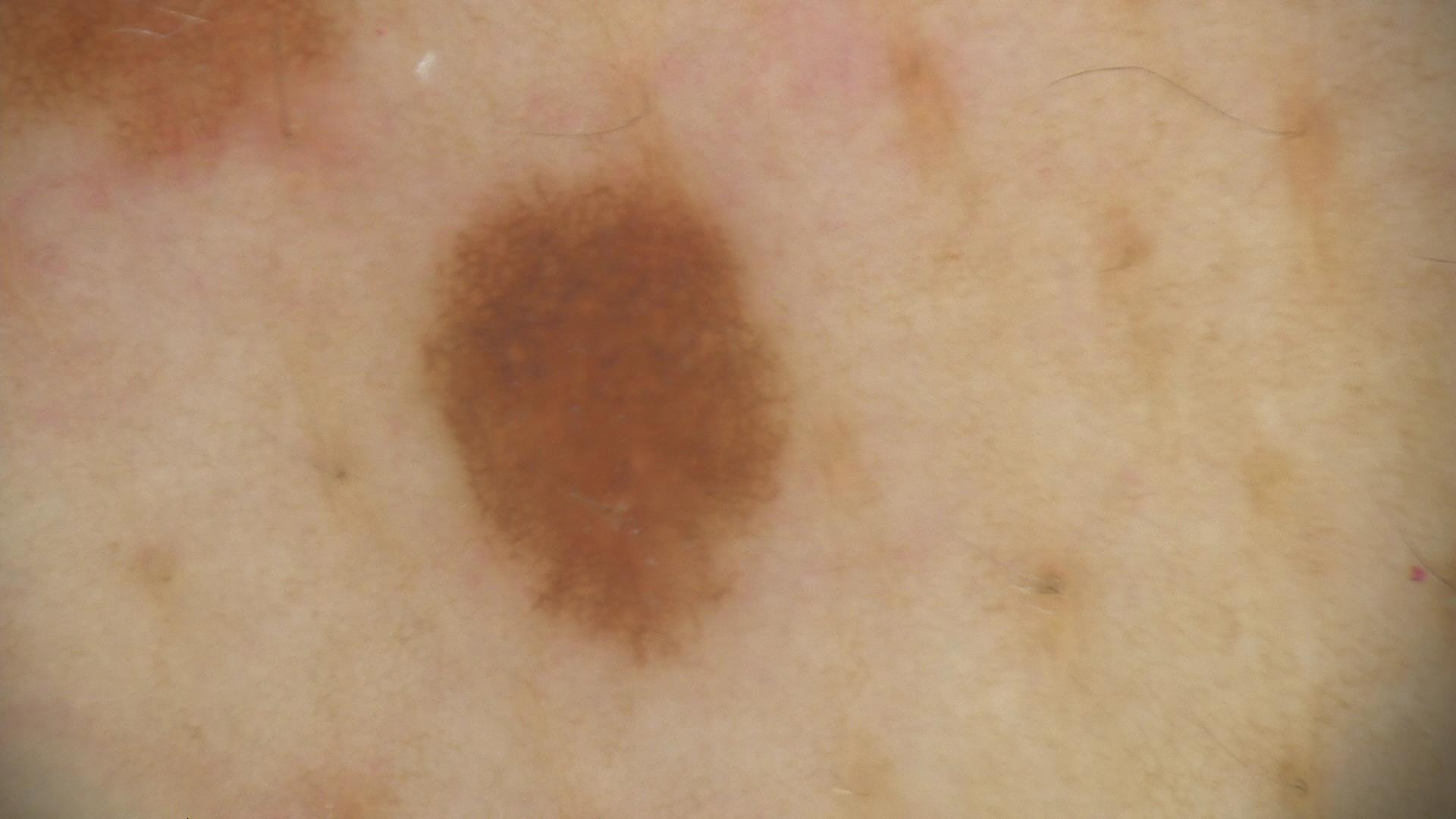The diagnostic label was a benign lesion — a dysplastic junctional nevus.